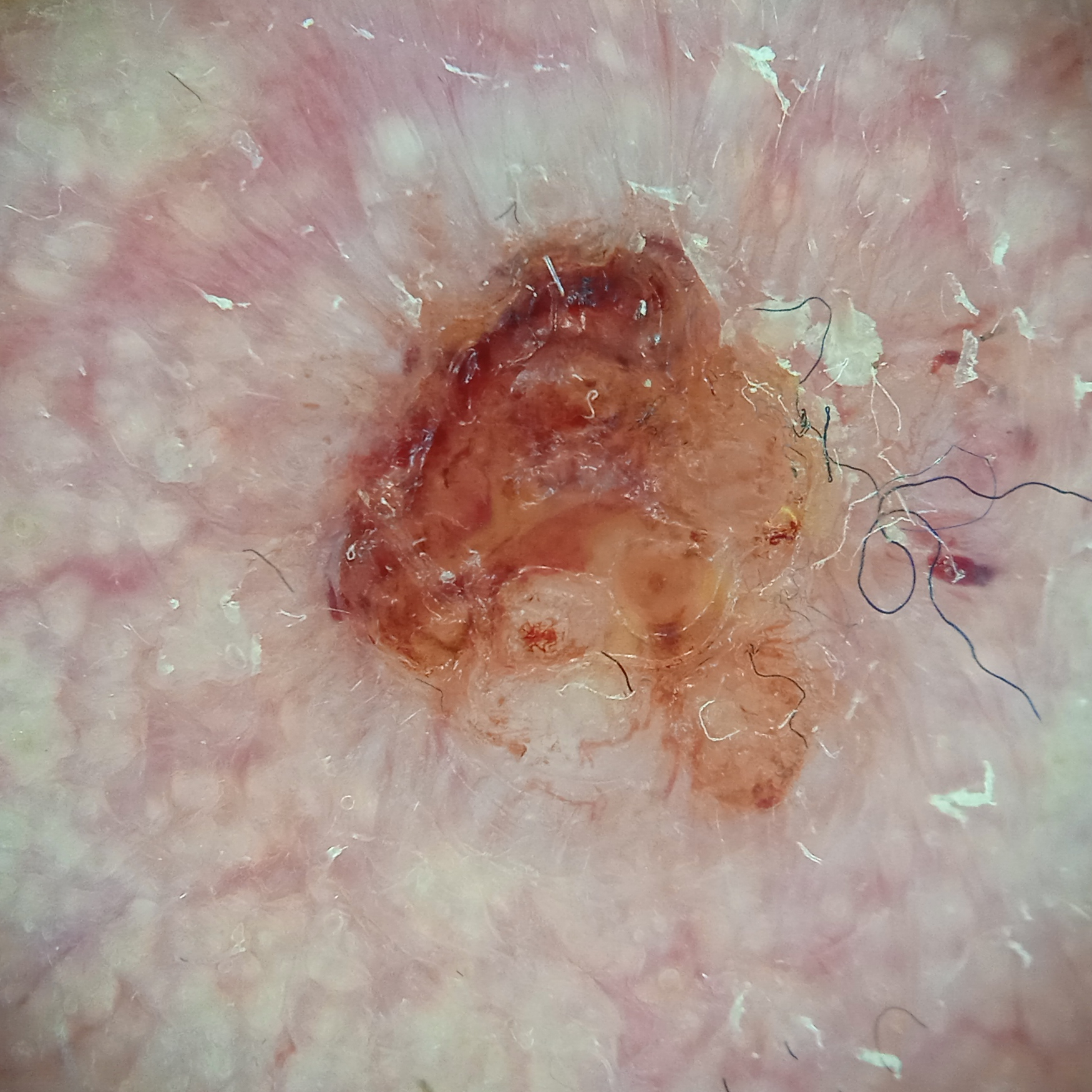image = dermatoscopic image | patient = male, aged 89 | sun reaction = skin reddens painfully with sun exposure | clinical context = clinical suspicion of basal cell carcinoma | site = the face | lesion size = 8.5 mm | pathology = basal cell carcinoma (biopsy-proven).